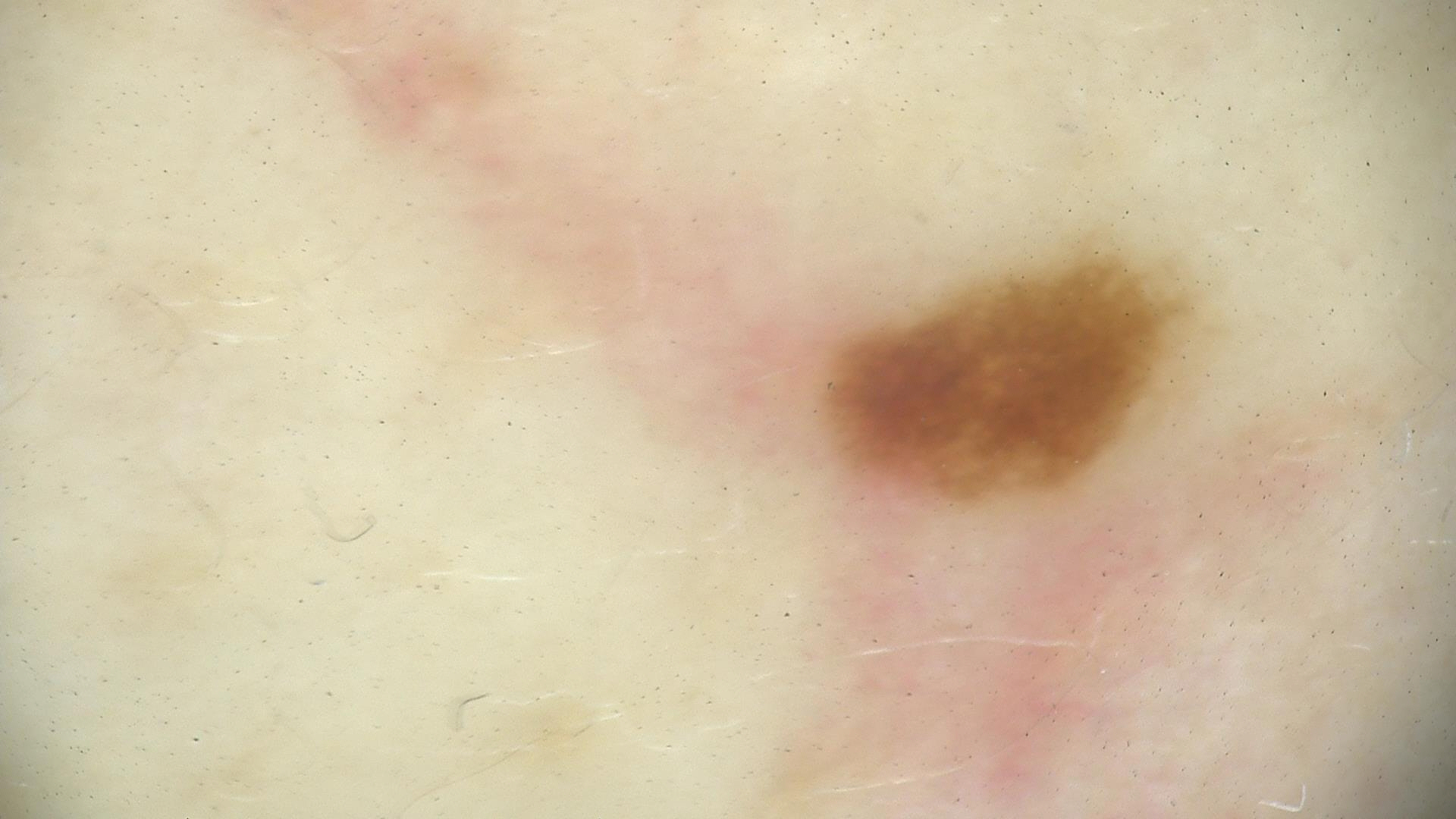Consistent with a dysplastic junctional nevus.